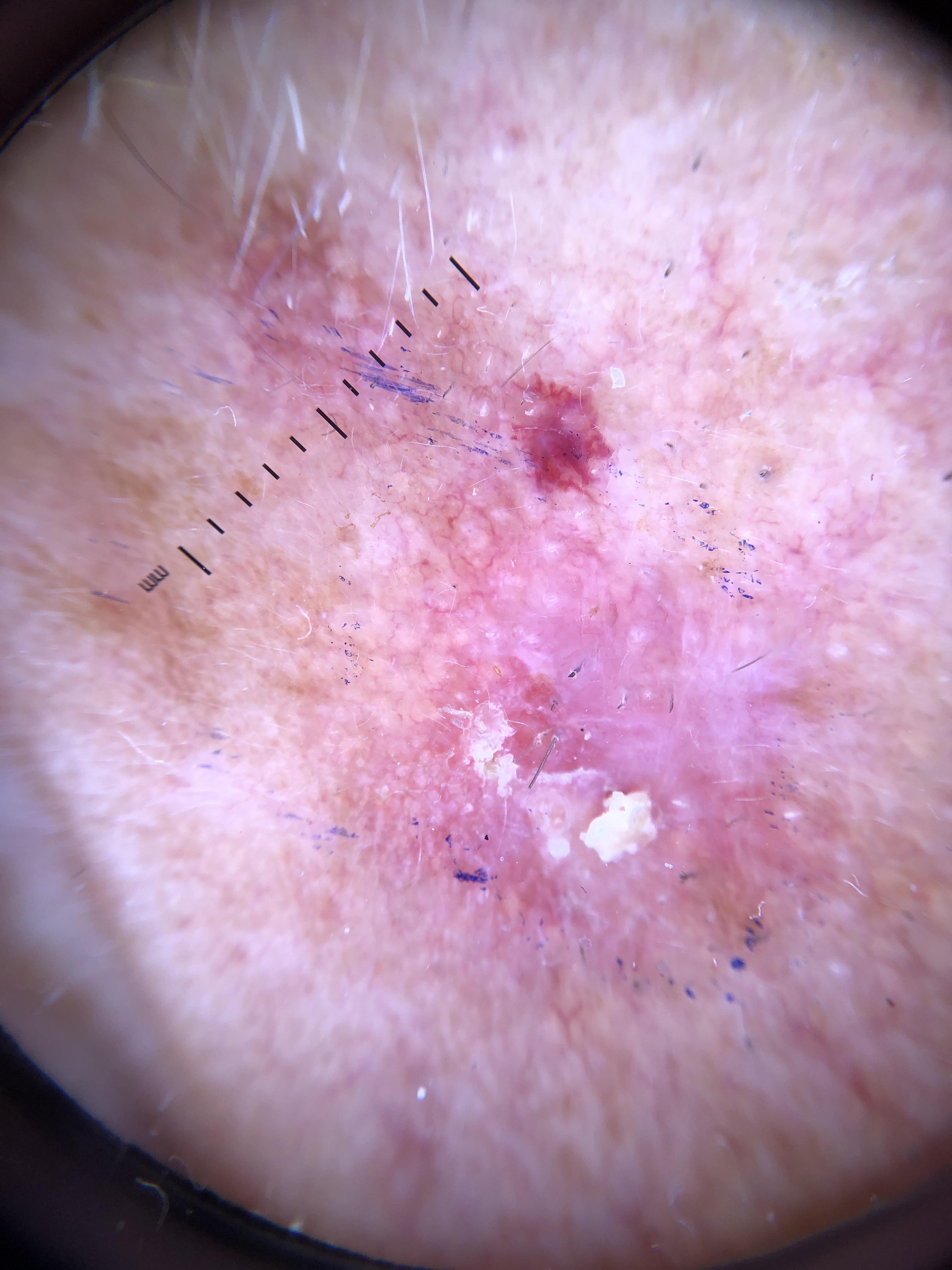Case summary: A dermoscopic image of a skin lesion. The patient was assessed as Fitzpatrick phototype I. The lesion is located on the head or neck. Conclusion: Histopathology confirmed an epidermal lesion — a squamous cell carcinoma.